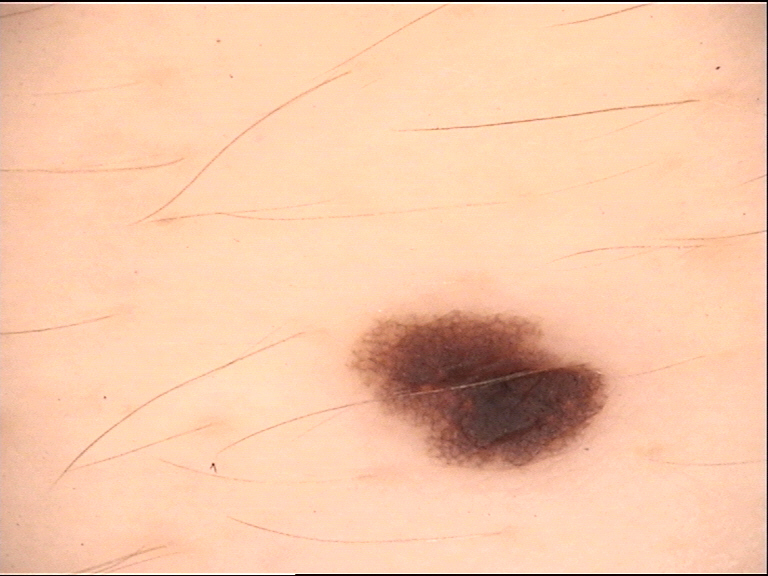Summary:
A dermoscopic close-up of a skin lesion.
Impression:
The diagnosis was a benign lesion — a dysplastic junctional nevus.